An image taken at a distance. The lesion involves the palm and arm.
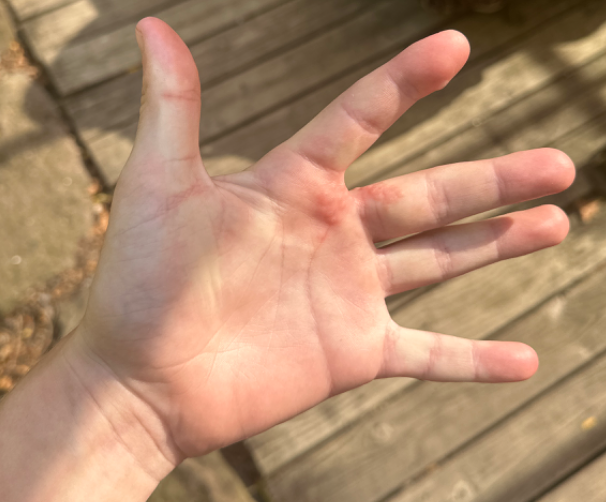The condition has been present for less than one week.
The contributor notes itching, burning and pain.
The reviewing dermatologist's impression was: the favored diagnosis is Herpes Simplex; also consider Allergic Contact Dermatitis; an alternative is Eczema.